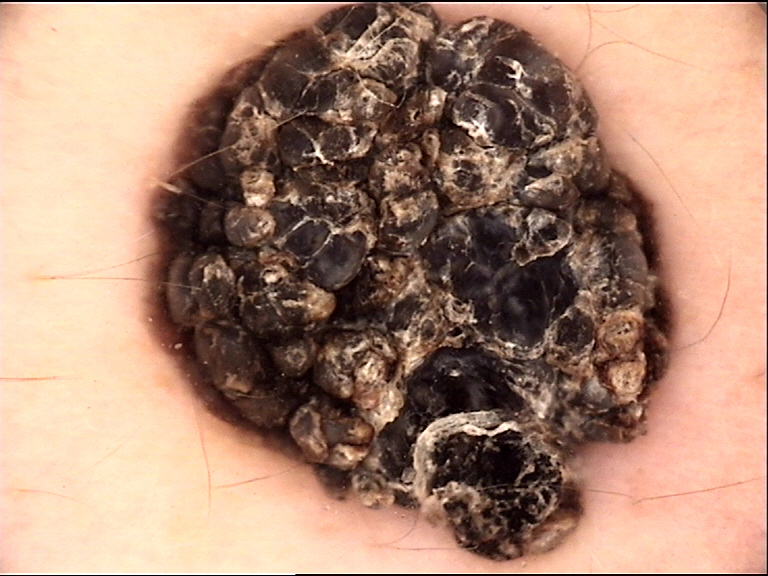diagnosis:
  name: melanoma
  code: mel
  malignancy: malignant
  super_class: melanocytic
  confirmation: histopathology